Located on the leg; this image was taken at an angle; the contributor is a female aged 40–49:
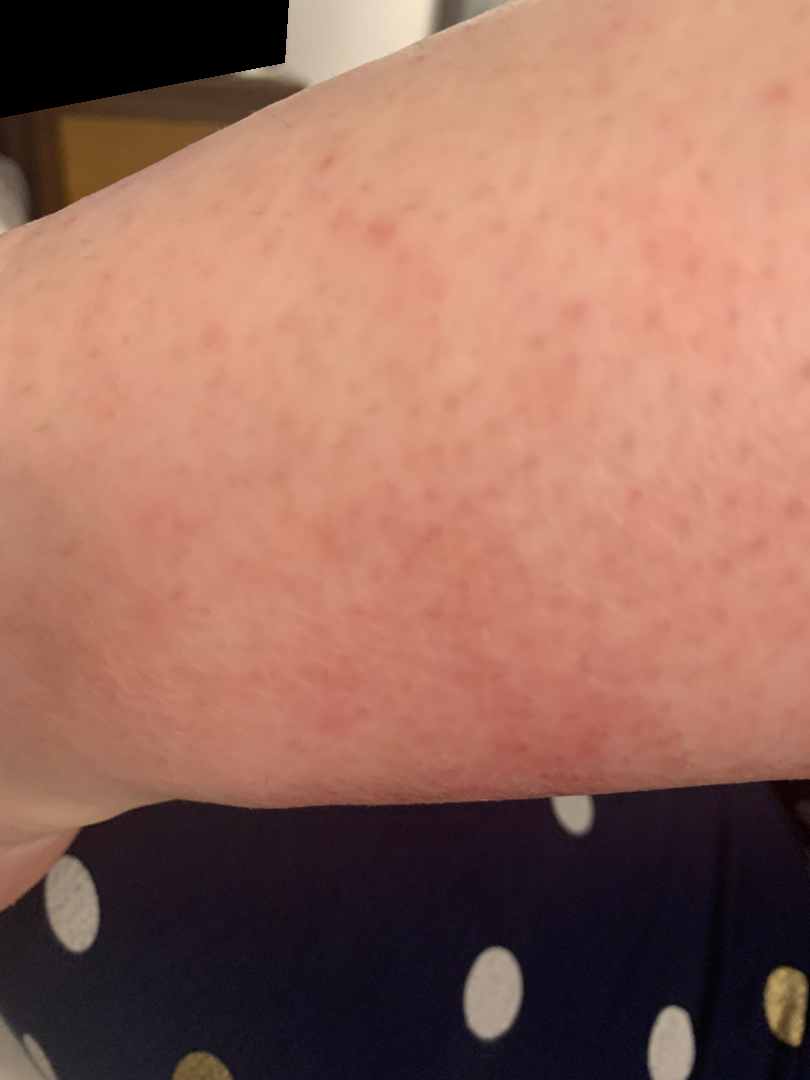On remote review of the image: Stasis Dermatitis (100%).